A skin lesion imaged with a dermatoscope.
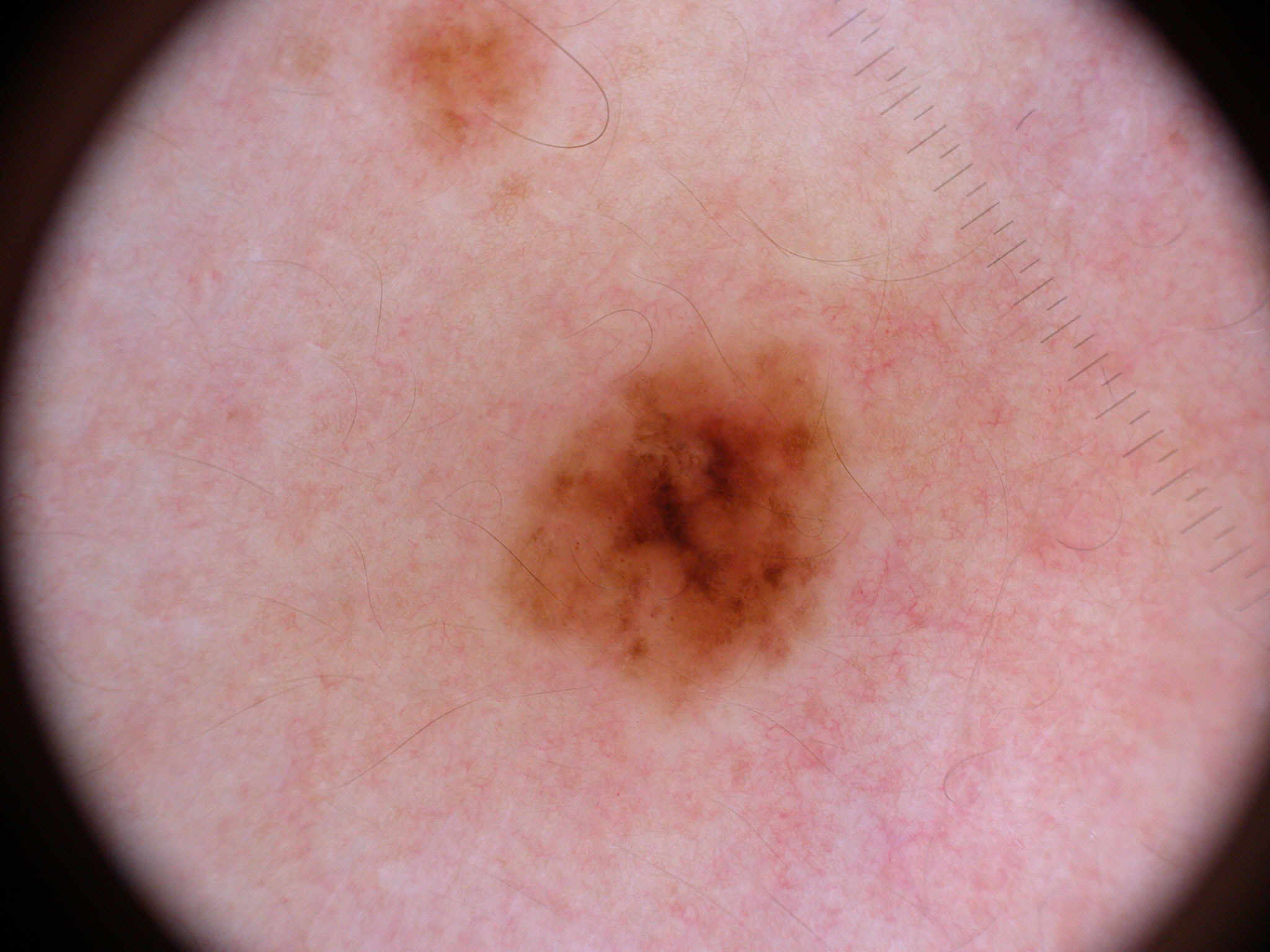lesion location = (500, 335, 859, 731) | dermoscopic pattern = pigment network | extent = ~8% of the field | impression = a melanocytic nevus.